A male subject aged 68-72; the patient is skin type II; per the chart, a prior melanoma; a dermoscopic close-up of a skin lesion:
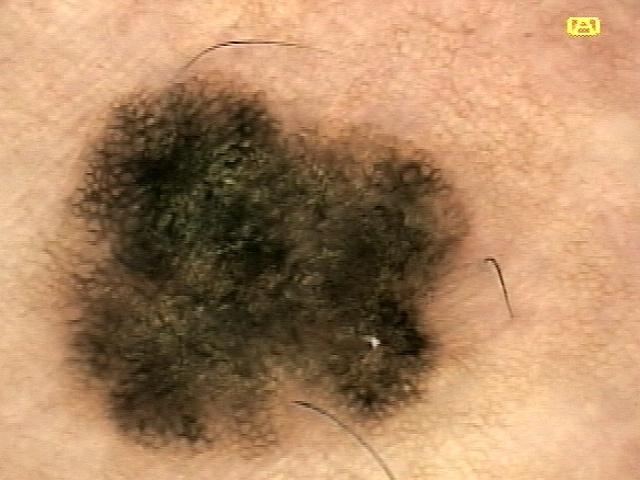Summary: Located on the posterior trunk. Diagnosis: Histopathology confirmed a malignancy — a melanoma.